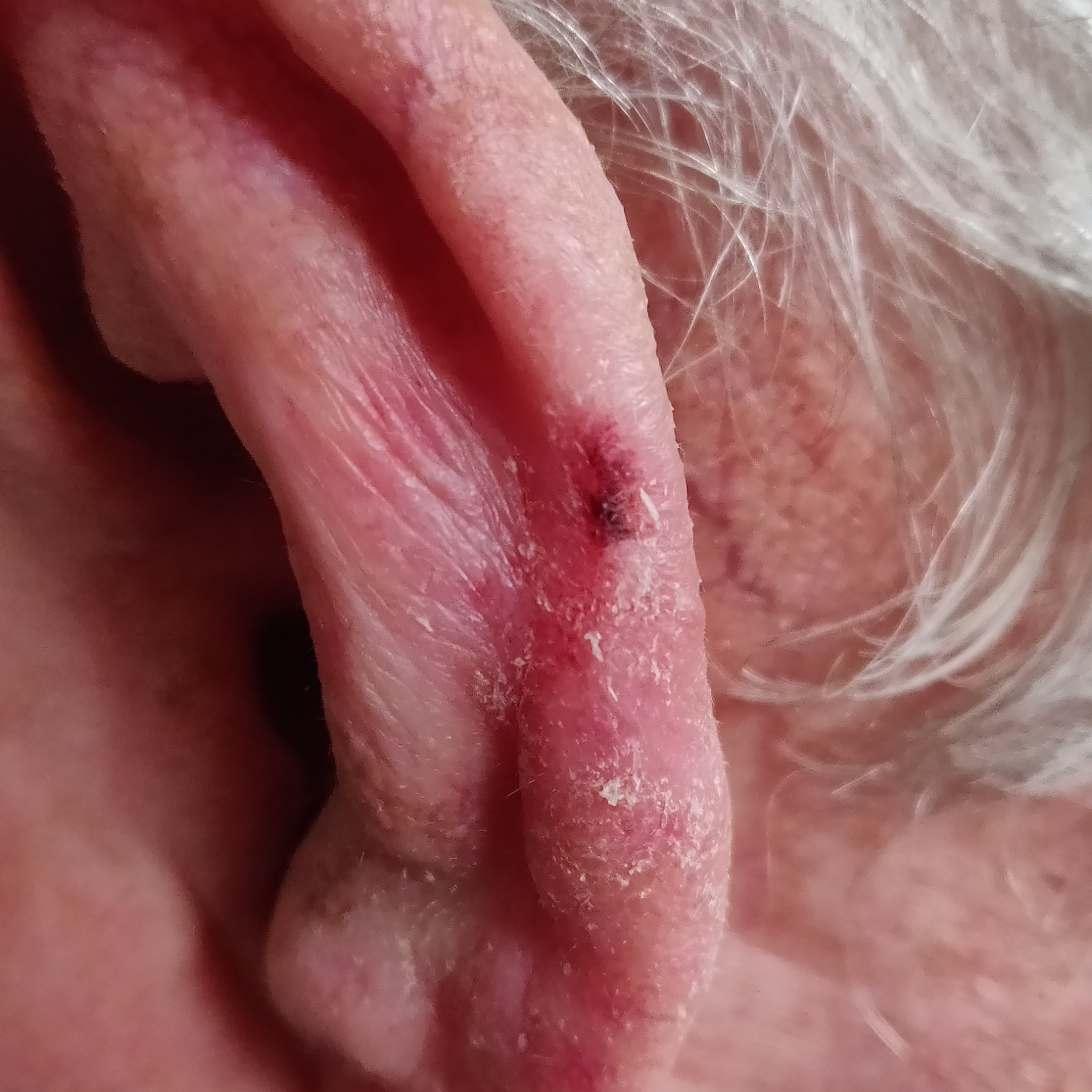Notes:
• risk factors · tobacco use, prior malignancy (patient or family), pesticide exposure
• image type · smartphone clinical photo
• patient · male, aged 71
• skin phototype · II
• body site · an ear
• lesion diameter · 30 × 20 mm
• patient-reported symptoms · growth, pain, bleeding, itching / no change in appearance, no elevation
• diagnostic label · actinic keratosis (biopsy-proven)